This is a dermoscopic photograph of a skin lesion.
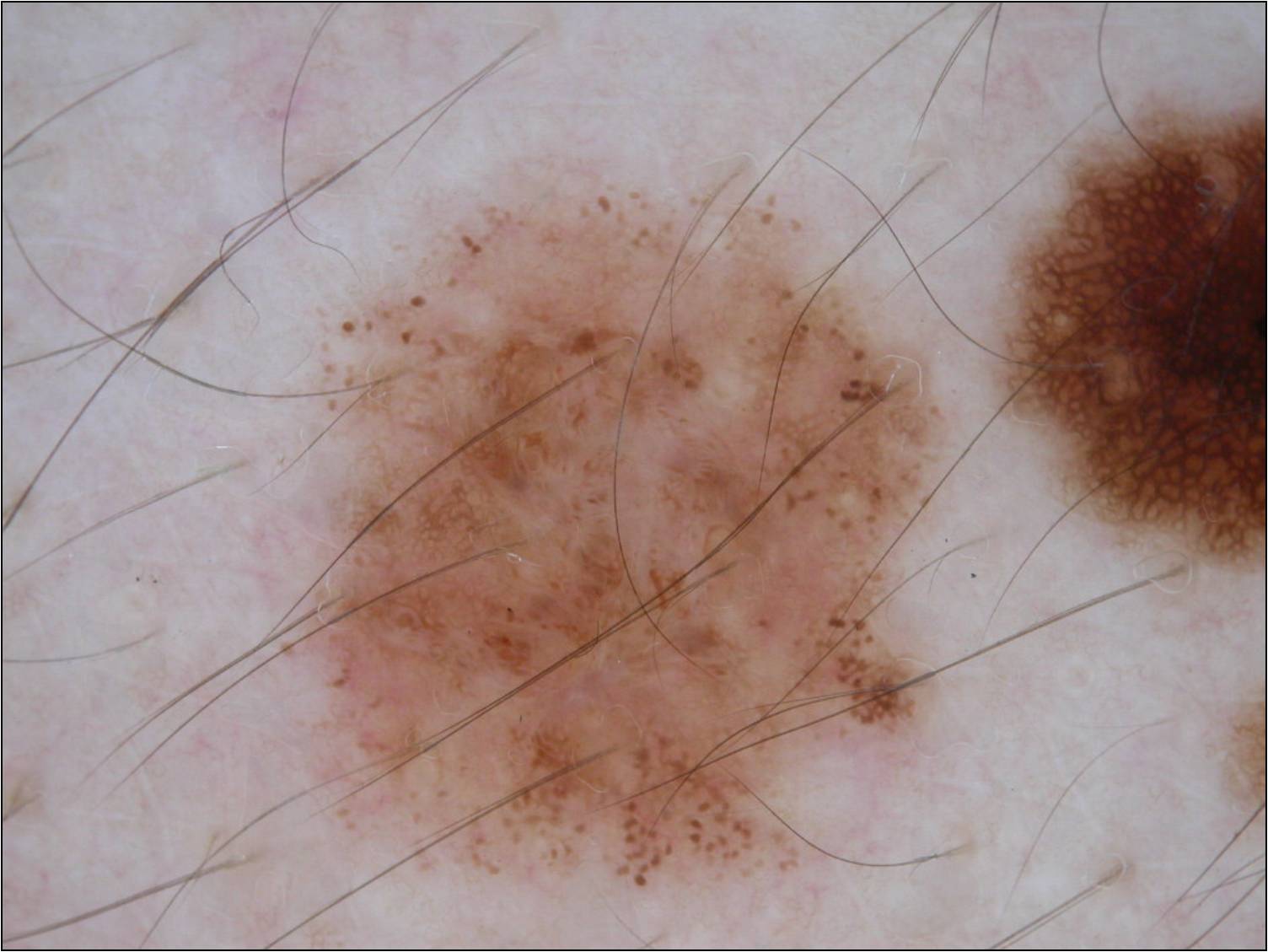Summary: With coordinates (x1, y1, x2, y2), the visible lesion spans 263, 163, 954, 896. Conclusion: The clinical diagnosis was a melanocytic nevus, a benign lesion.